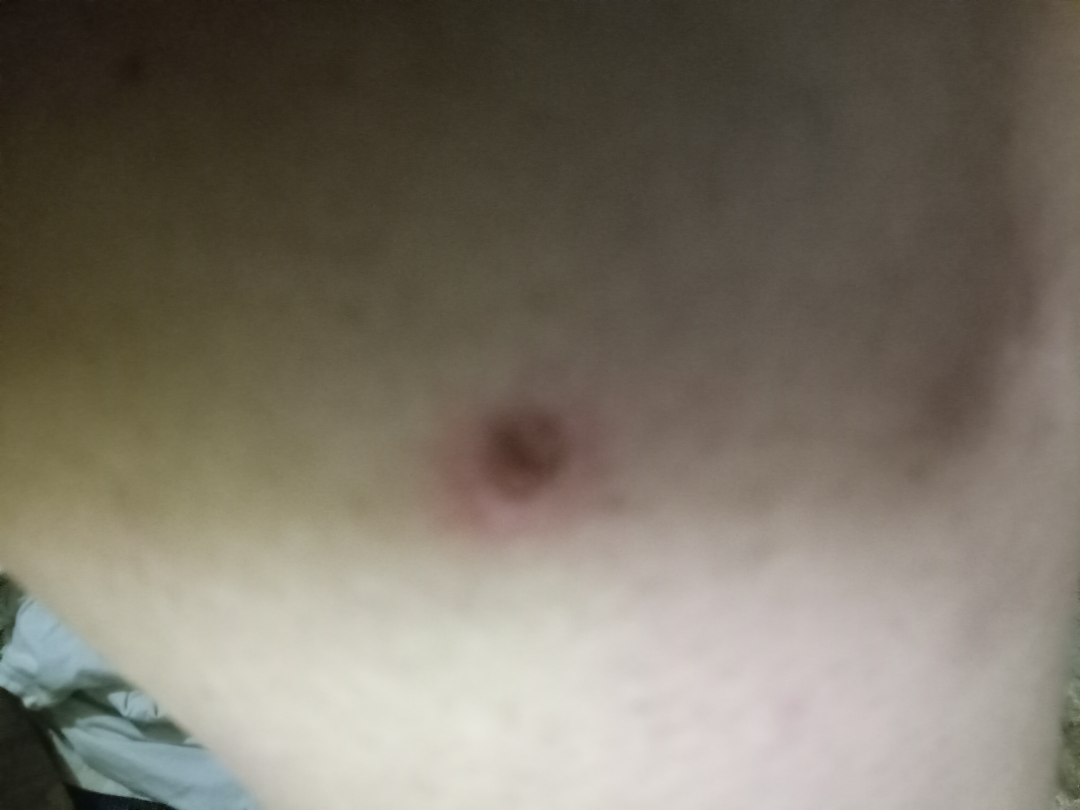Assessment: The case was indeterminate on photographic review. Clinical context: Close-up view.